A skin lesion imaged with a dermatoscope.
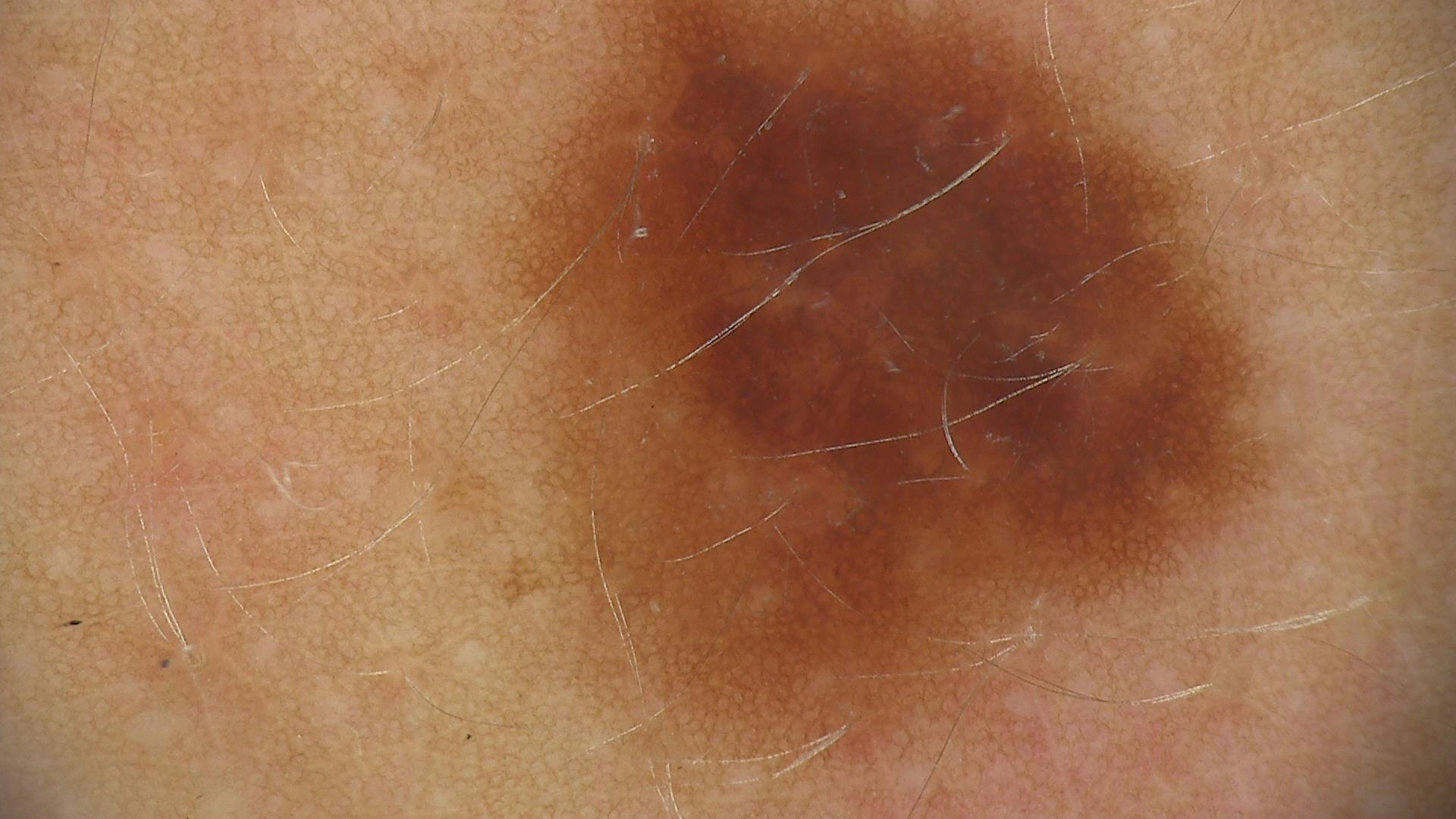{
  "diagnosis": {
    "name": "dysplastic junctional nevus",
    "code": "jd",
    "malignancy": "benign",
    "super_class": "melanocytic",
    "confirmation": "expert consensus"
  }
}